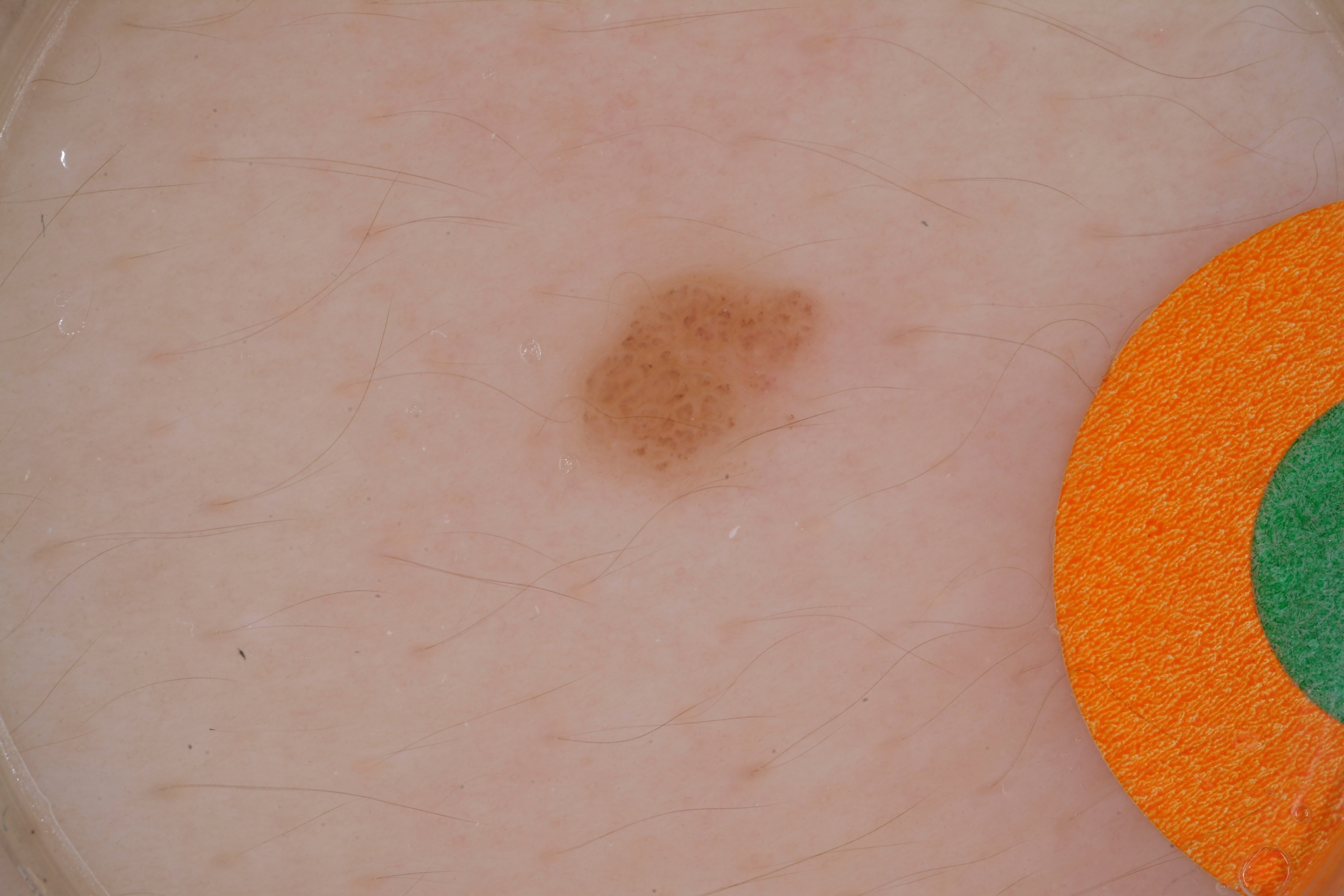A dermoscopic close-up of a skin lesion.
The patient is a male aged 13 to 17.
A small lesion occupying a minor part of the field.
Dermoscopic examination shows globules.
With coordinates (x1, y1, x2, y2), the lesion's extent is 582 273 835 483.
The lesion was assessed as a melanocytic nevus, a benign lesion.